A dermoscopy image of a single skin lesion. A male subject aged approximately 70 — 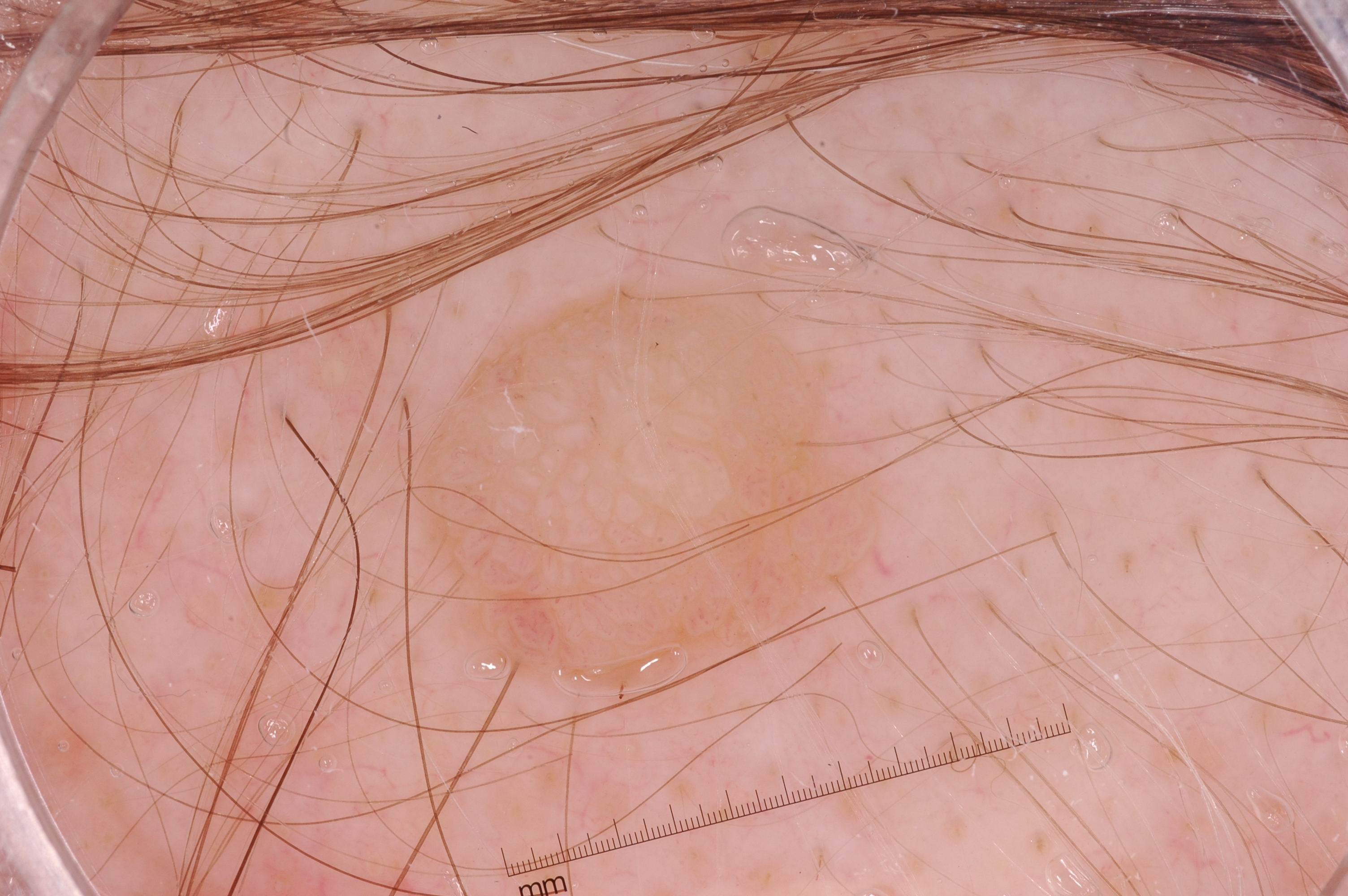  lesion_location:
    bbox_xyxy:
      - 410
      - 270
      - 906
      - 690
  lesion_extent: moderate
  dermoscopic_features:
    present: []
    absent:
      - negative network
      - pigment network
      - streaks
      - milia-like cysts
  diagnosis:
    name: seborrheic keratosis
    malignancy: benign
    lineage: keratinocytic
    provenance: clinical